A dermoscopic close-up of a skin lesion.
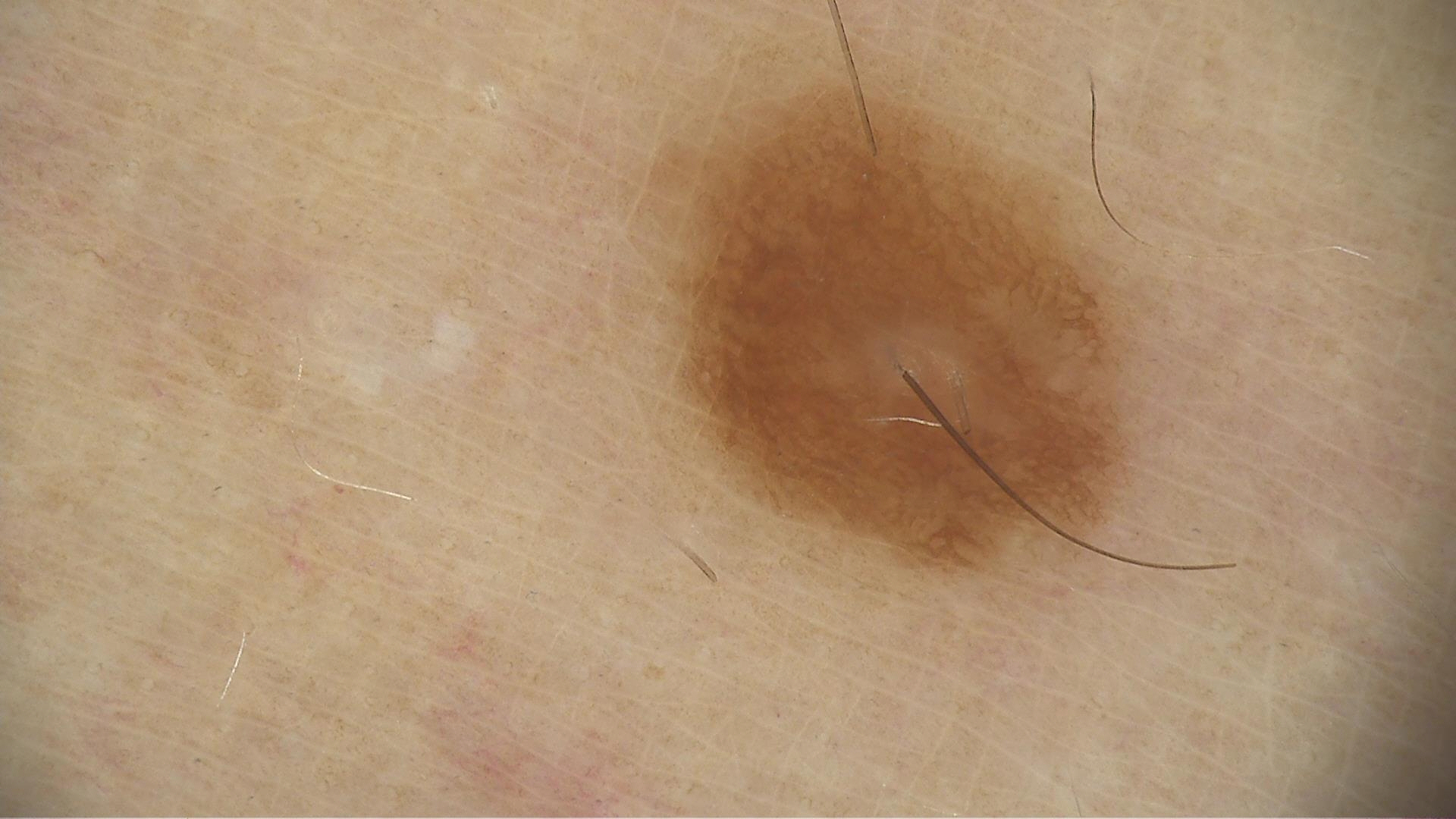{"diagnosis": {"name": "compound nevus", "code": "cb", "malignancy": "benign", "super_class": "melanocytic", "confirmation": "expert consensus"}}